A dermoscopic image of a skin lesion.
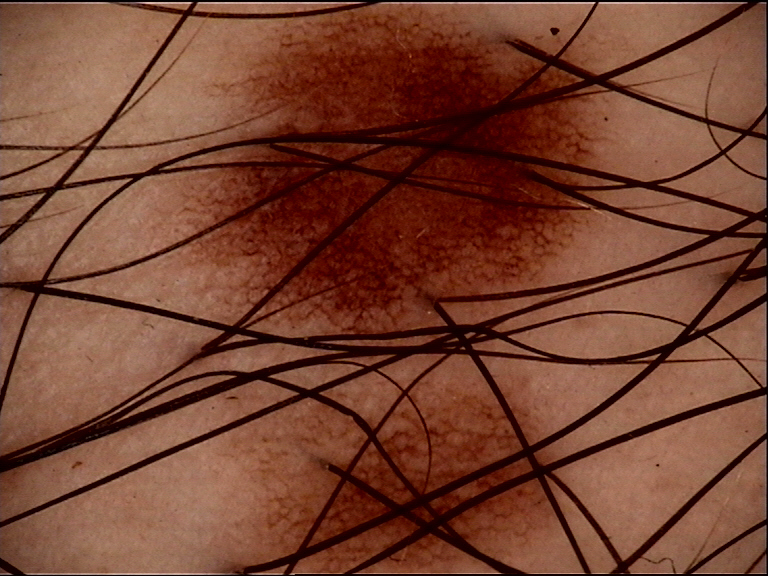Diagnosed as a dysplastic junctional nevus.